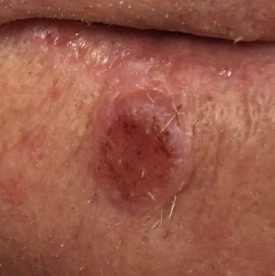Findings: The patient was assessed as Fitzpatrick II. A clinical close-up photograph of a skin lesion. A male patient age 66. The lesion was found on the face. Measuring about 12 × 10 mm. The patient reports that the lesion hurts, has bled, itches, has grown, and is elevated. Diagnosis: Histopathologically confirmed as a malignant skin lesion — a squamous cell carcinoma.